A female patient, in their 50s; a dermoscopic close-up of a skin lesion:
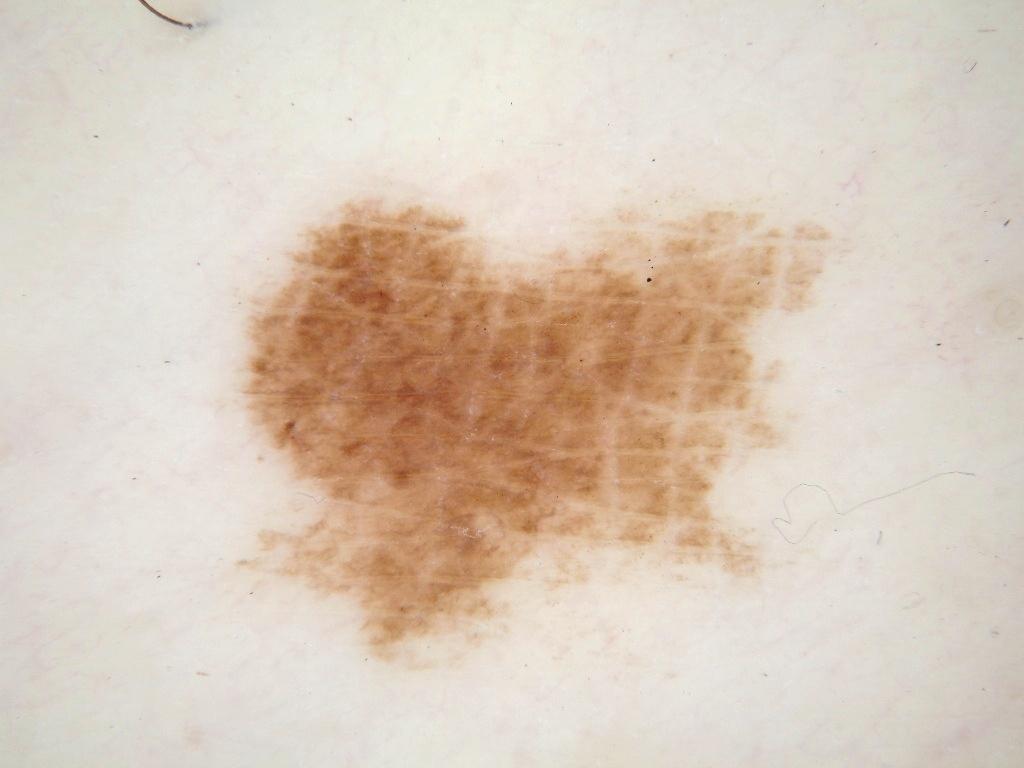{"lesion_location": {"bbox_xyxy": [204, 178, 840, 704]}, "dermoscopic_features": {"present": [], "absent": ["negative network", "globules", "pigment network", "milia-like cysts", "streaks"]}, "diagnosis": {"name": "melanocytic nevus", "malignancy": "benign", "lineage": "melanocytic", "provenance": "clinical"}}